A subject 57 years old — 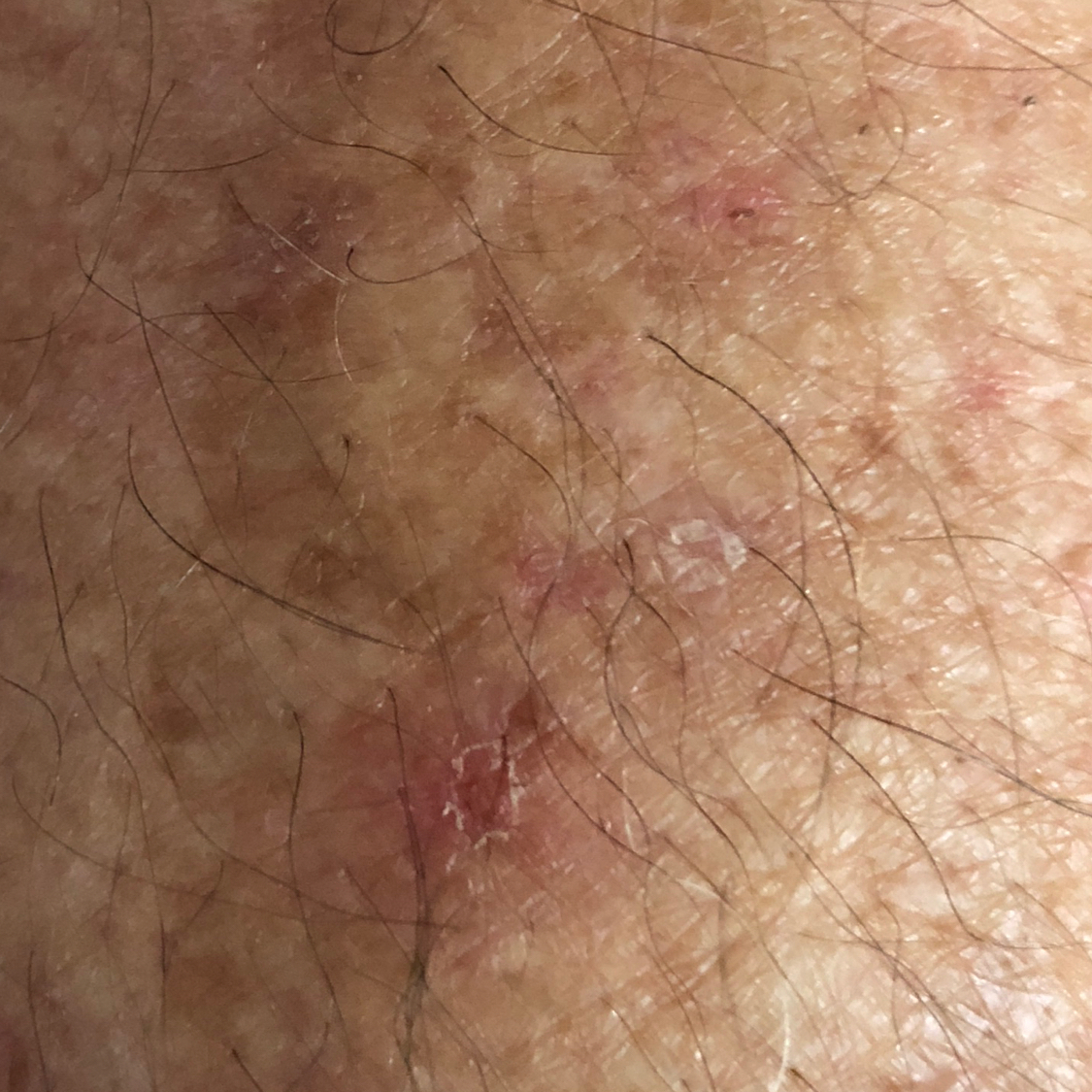The lesion involves a forearm.
The patient describes that the lesion has grown and itches, but is not elevated.
Diagnosed by dermatologist consensus as an actinic keratosis.